A dermoscopic image of a skin lesion.
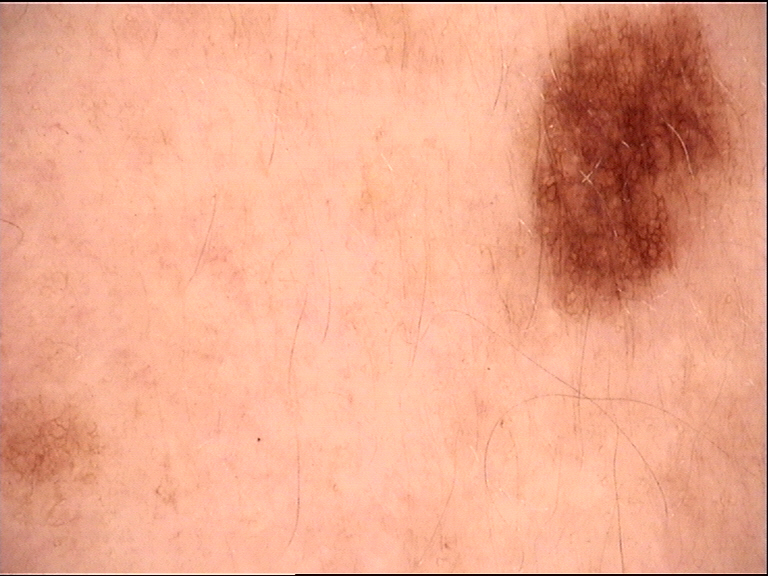Classified as a dysplastic junctional nevus.